A dermoscopic image of a skin lesion:
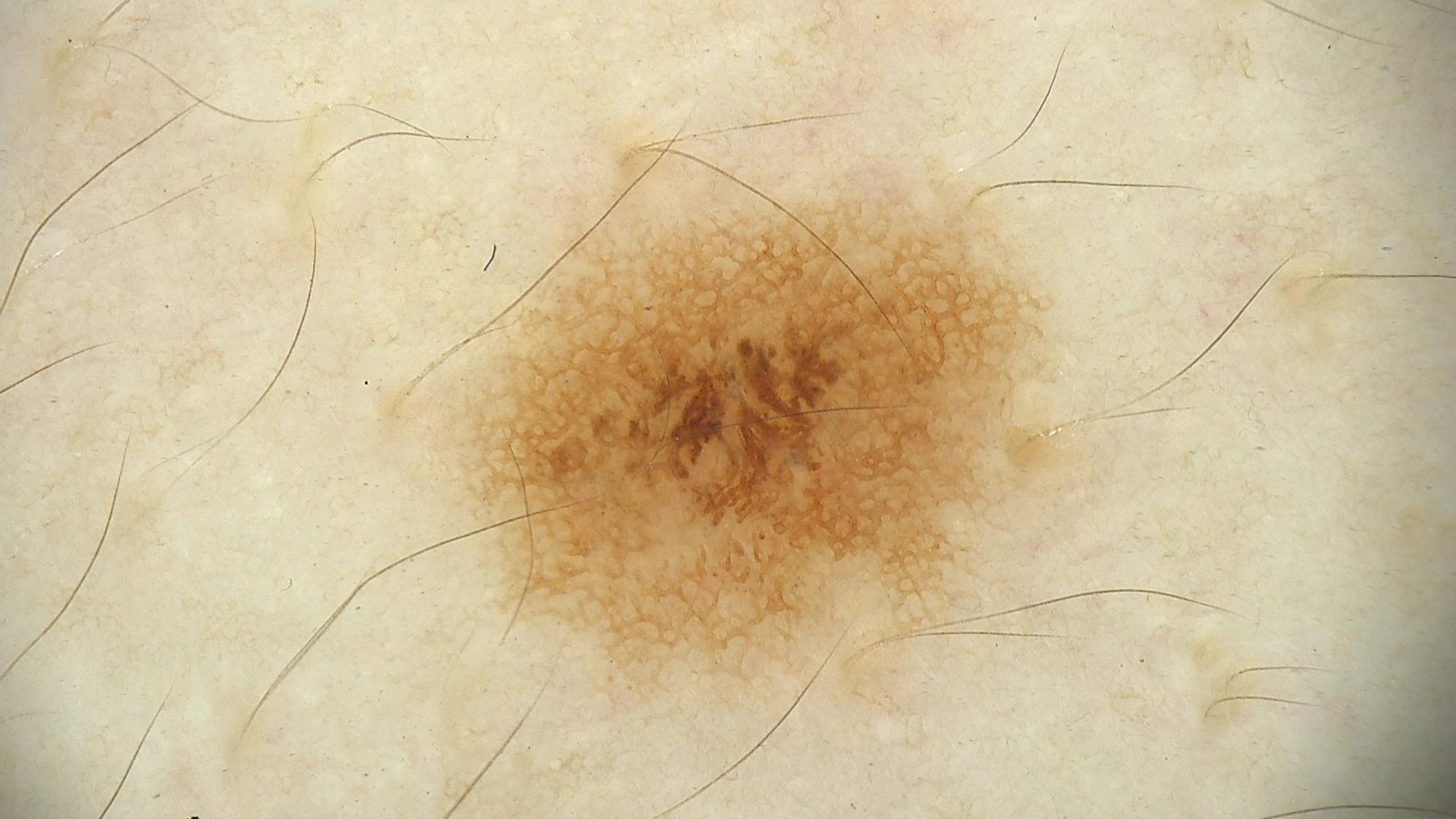The diagnostic label was a dysplastic junctional nevus.